The photo was captured at an angle. The patient reports pain and burning. The contributor is a male aged 50–59. The patient reports the condition has been present for less than one week. The lesion is described as rough or flaky, fluid-filled and raised or bumpy. The patient also reports fatigue. The patient described the issue as a rash: 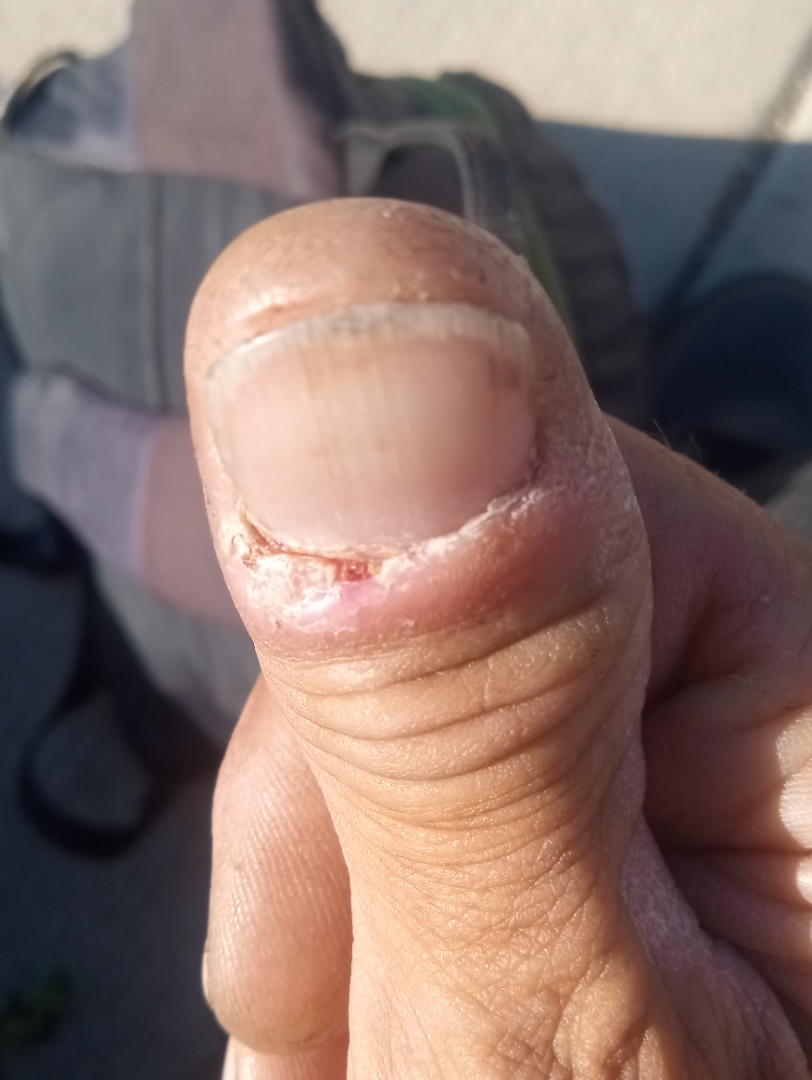Findings:
- impression: consistent with Paronychia